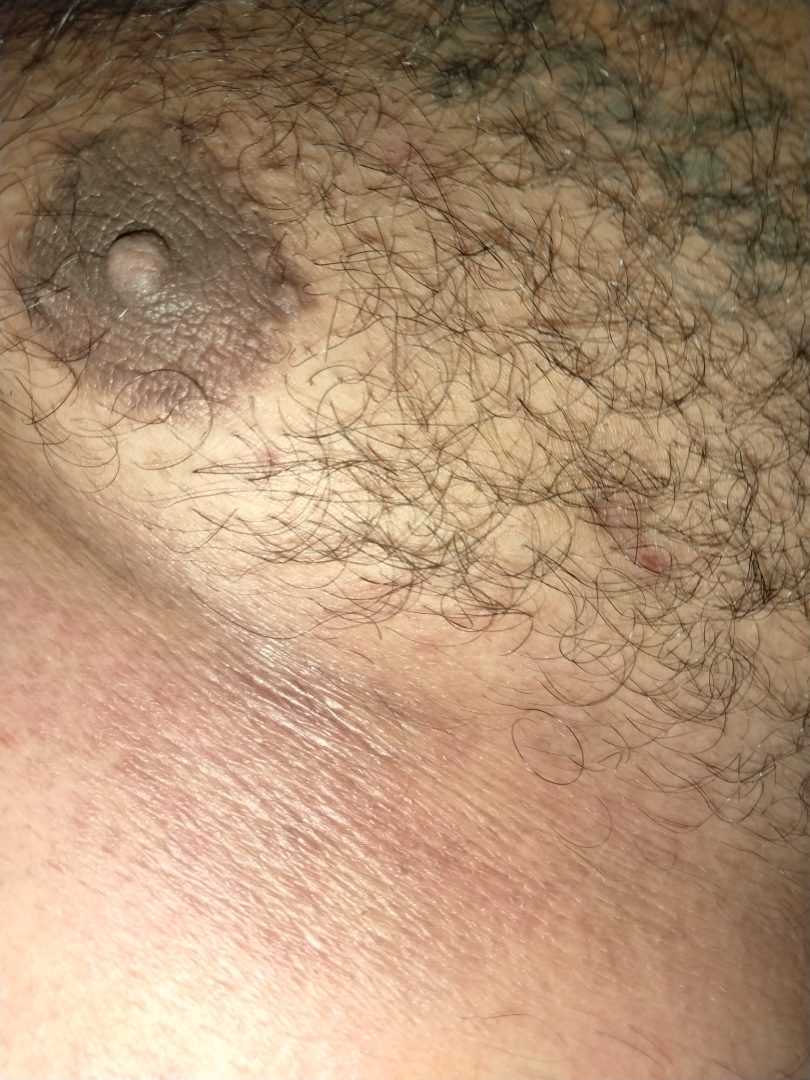- image framing — close-up
- patient — male, age 40–49
- differential — three independent reviewers: the impression was split between Acanthosis nigricans and Eczema; a remote consideration is Intertrigo; less likely is Contact dermatitis, NOS